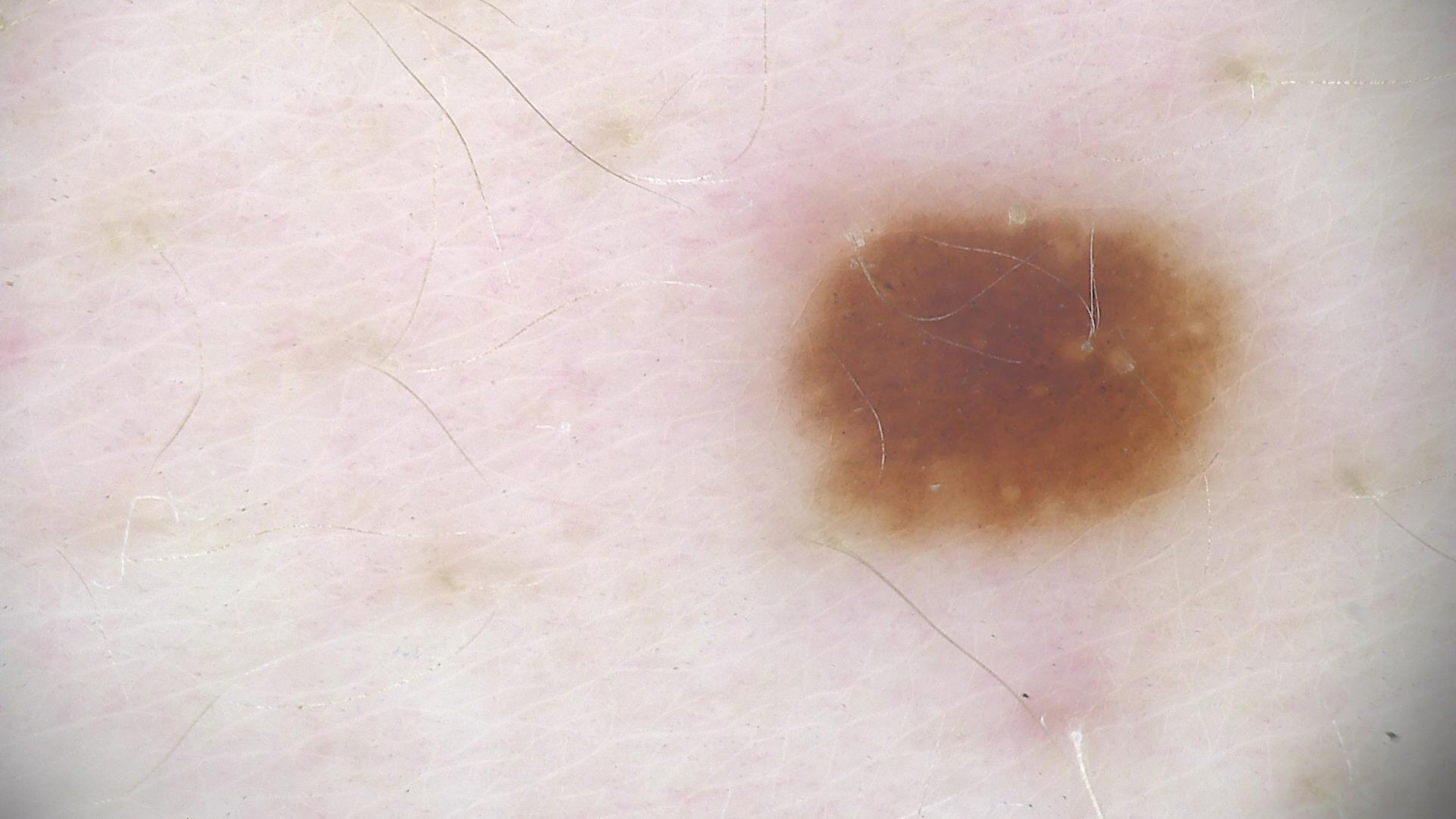diagnosis = dysplastic junctional nevus (expert consensus).